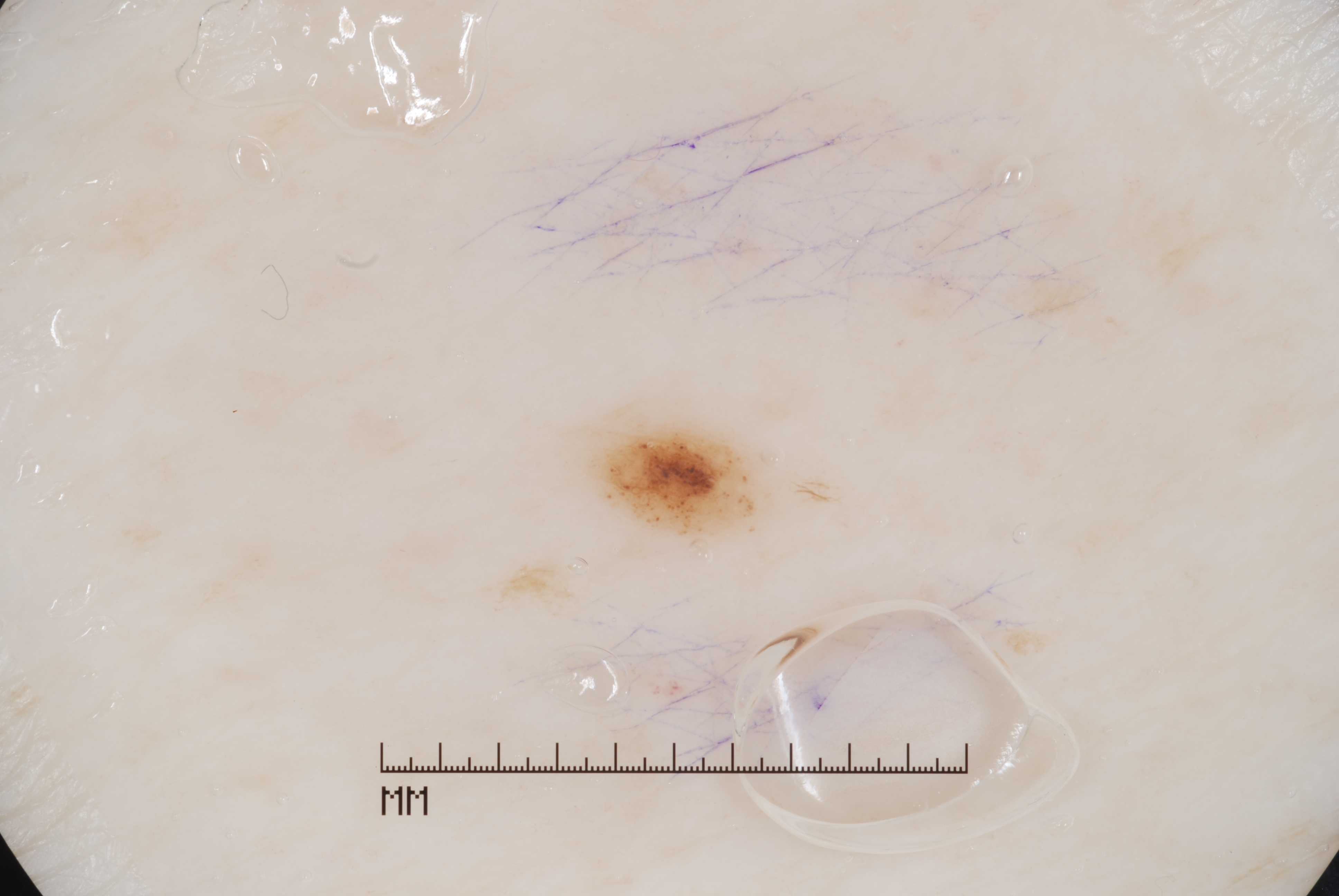A male patient aged 78 to 82. A dermoscopy image of a single skin lesion. With coordinates (x1, y1, x2, y2), the lesion's extent is box(586, 413, 753, 532). Dermoscopy demonstrates no milia-like cysts, negative network, pigment network, or streaks. Diagnosed as a melanocytic nevus, a benign skin lesion.